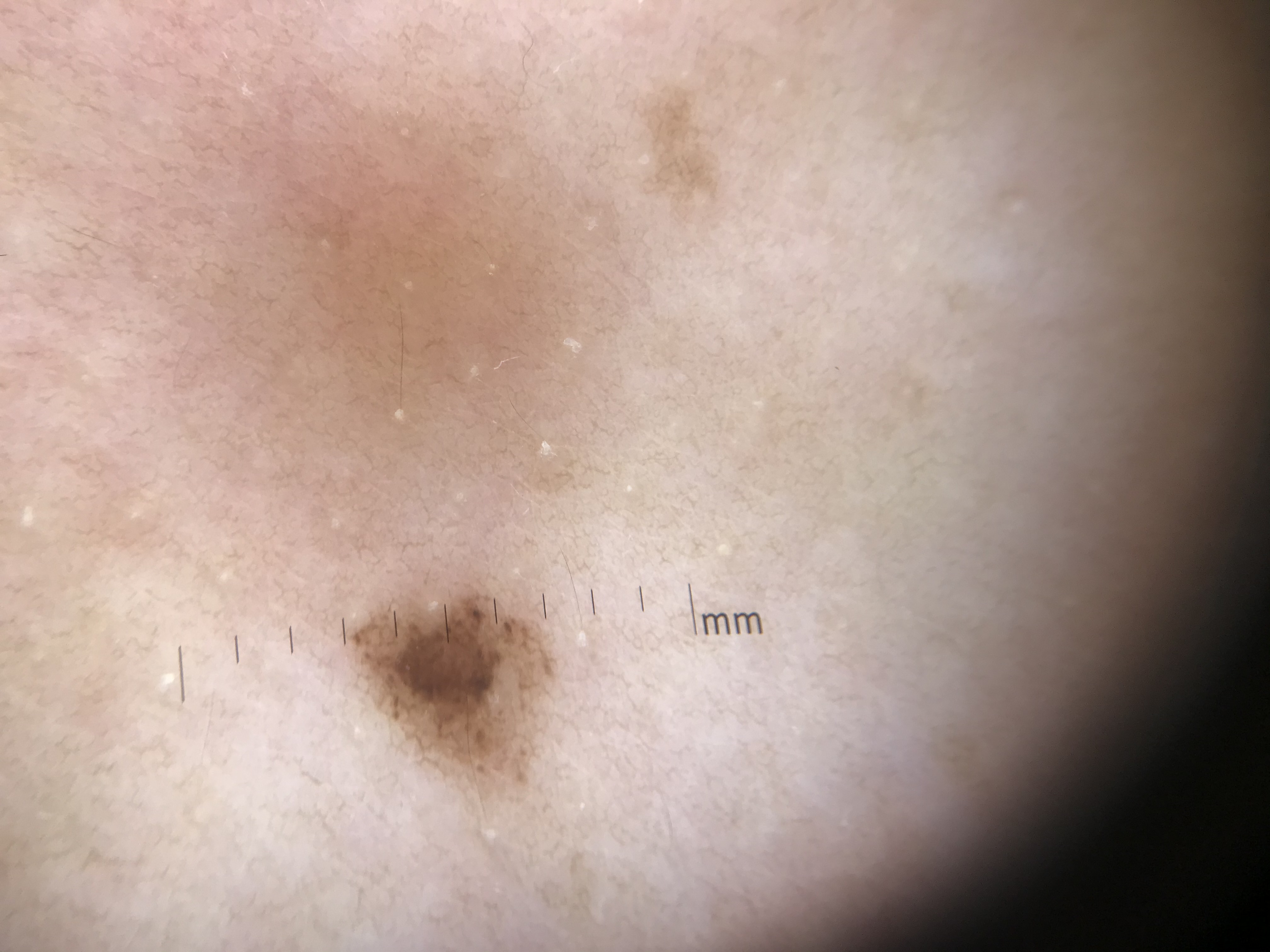Q: What is the diagnosis?
A: dysplastic junctional nevus (expert consensus)